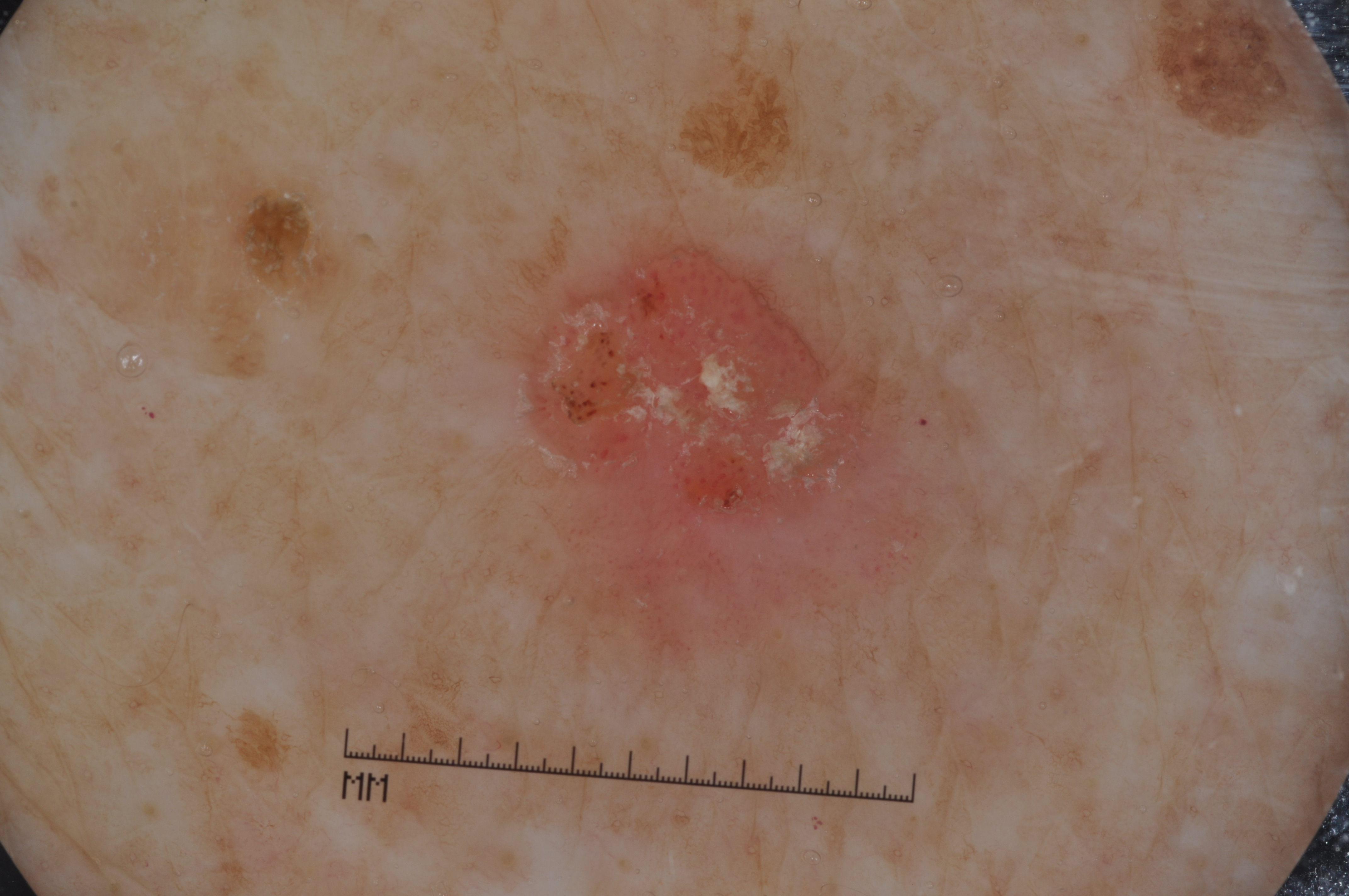A dermoscopic image of a skin lesion. Dermoscopic review identifies no streaks, pigment network, milia-like cysts, or negative network. As (left, top, right, bottom), the lesion is bounded by bbox=[506, 224, 970, 672]. The lesion takes up a moderate portion of the field. The diagnostic assessment was a seborrheic keratosis.